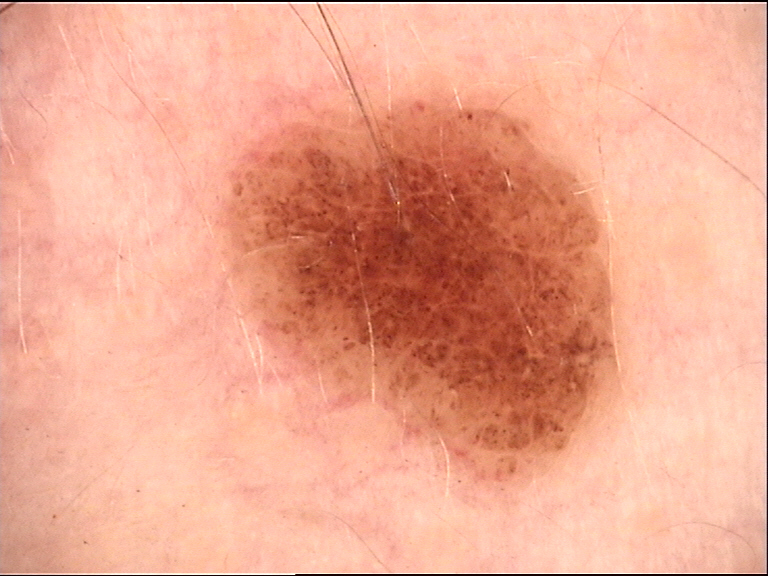Consistent with a benign lesion — a dysplastic compound nevus.